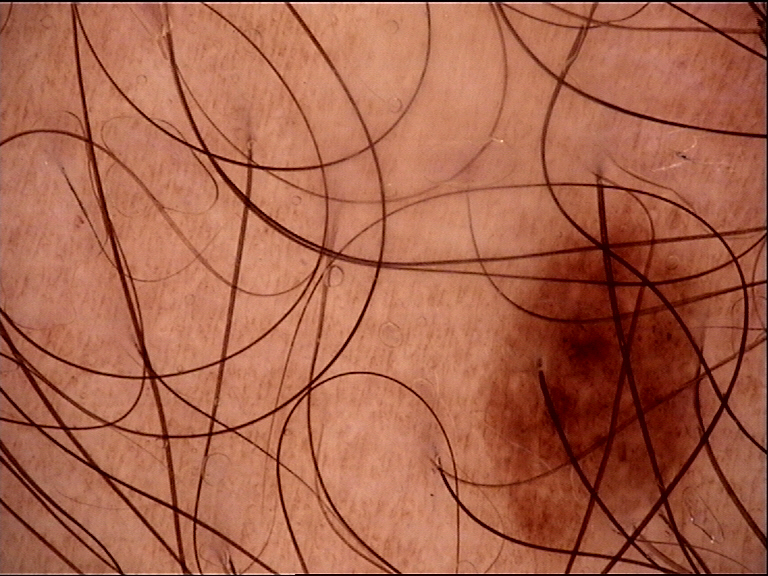Findings:
• class — dysplastic compound nevus (expert consensus)